The affected area is the leg. The photograph was taken at an angle. Self-categorized by the patient as a rash. Symptoms reported: itching. Female patient, age 18–29. No constitutional symptoms were reported. The patient notes the condition has been present for less than one week — 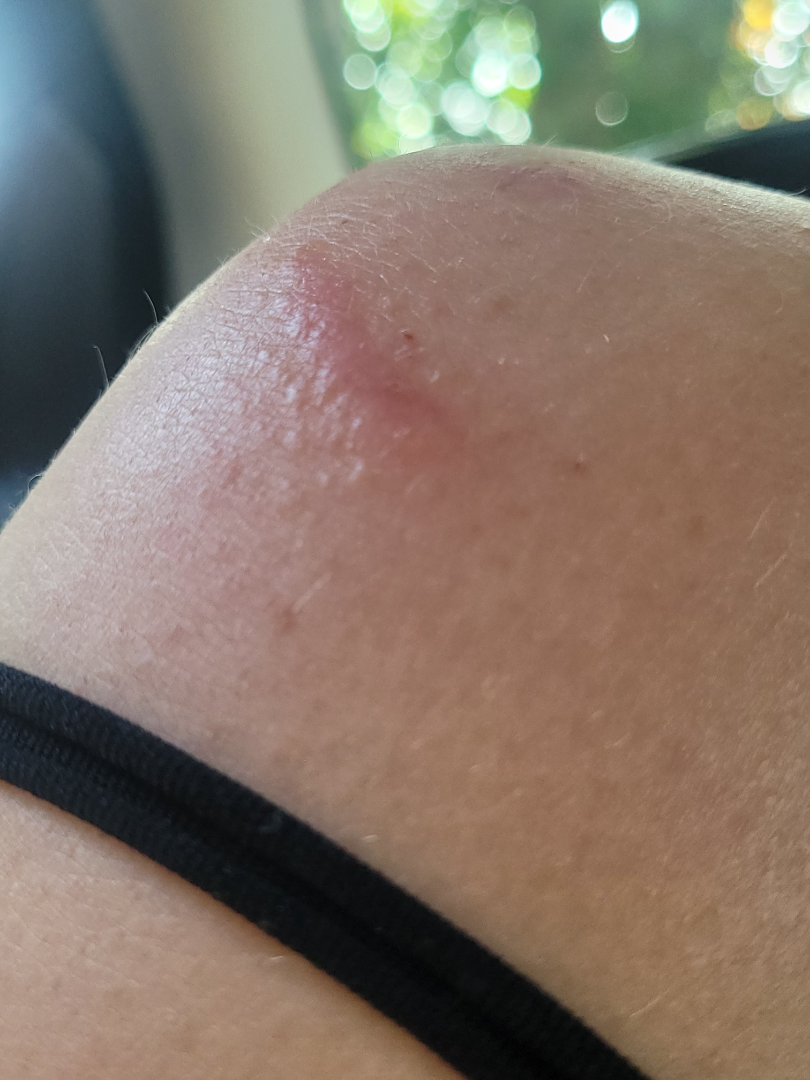No differential diagnosis could be assigned on photographic review.